A skin lesion imaged with a dermatoscope.
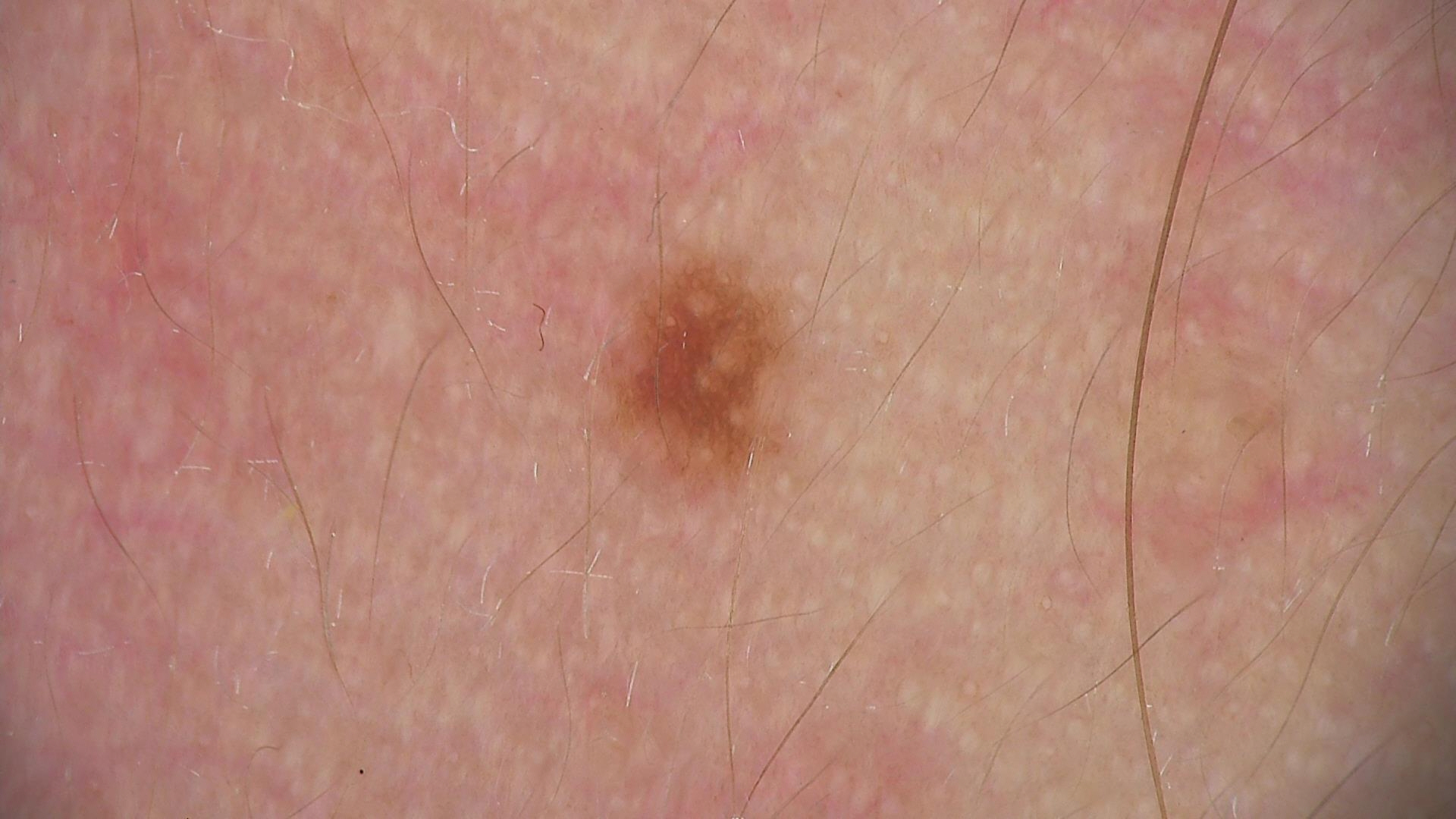This is a banal lesion.
Classified as a junctional nevus.